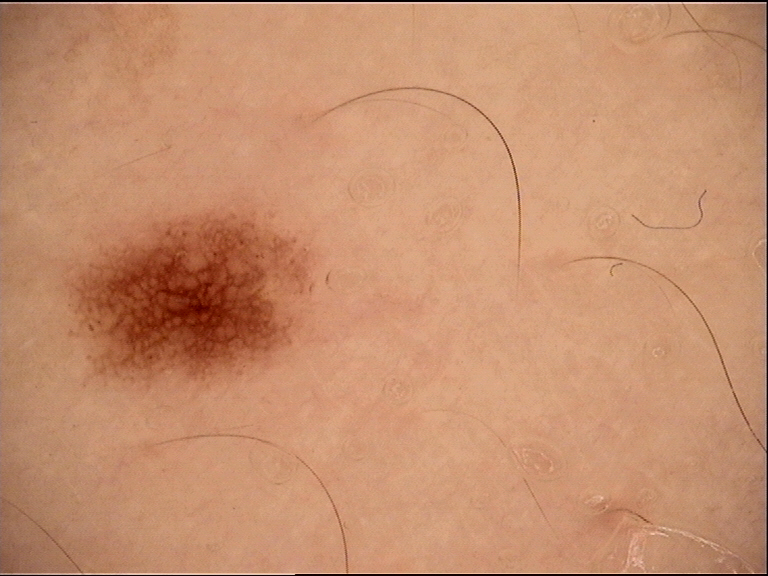Findings: A dermoscopic close-up of a skin lesion. Conclusion: Classified as a benign lesion — a dysplastic junctional nevus.